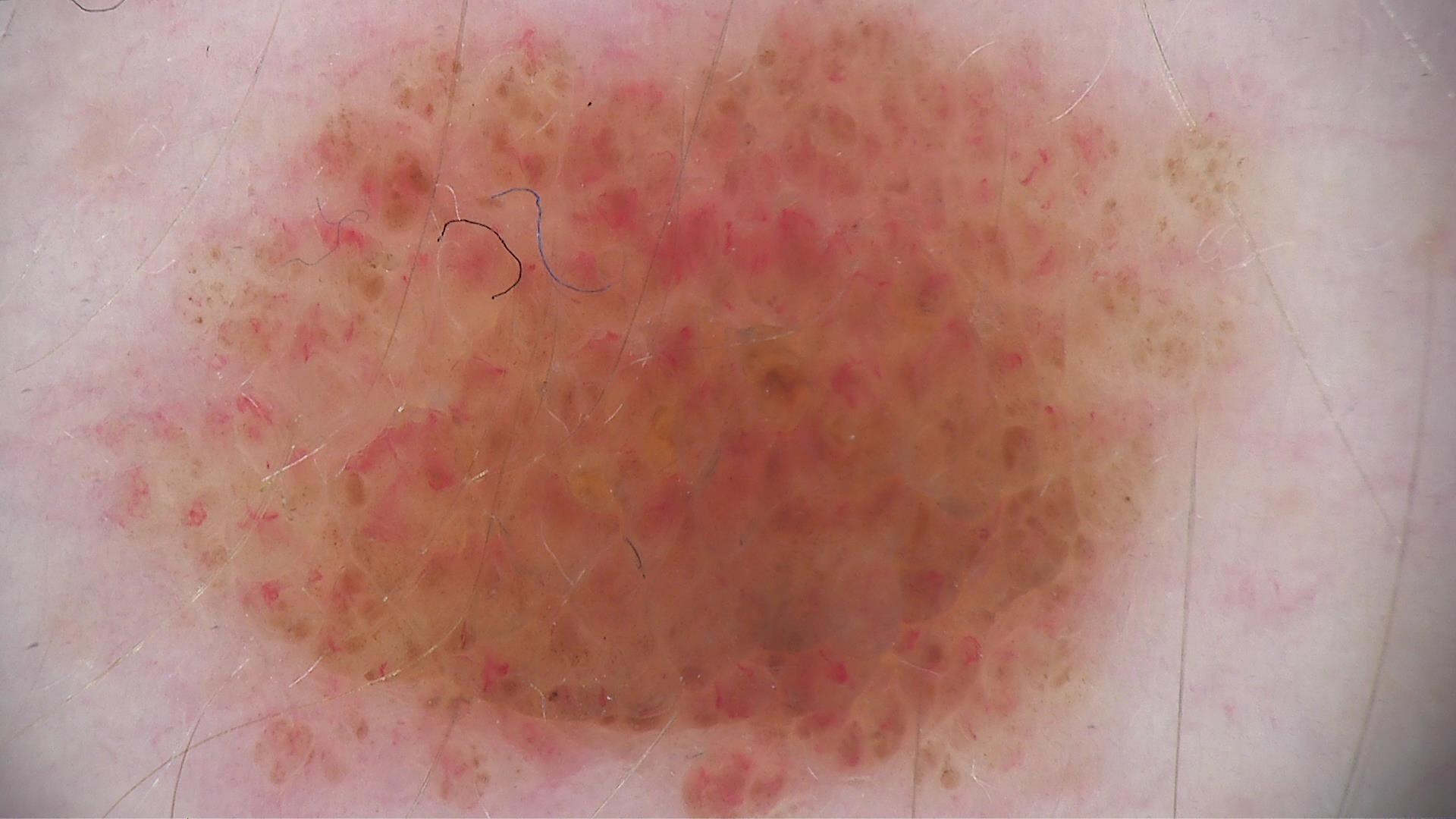The diagnostic label was a banal lesion — a compound nevus.